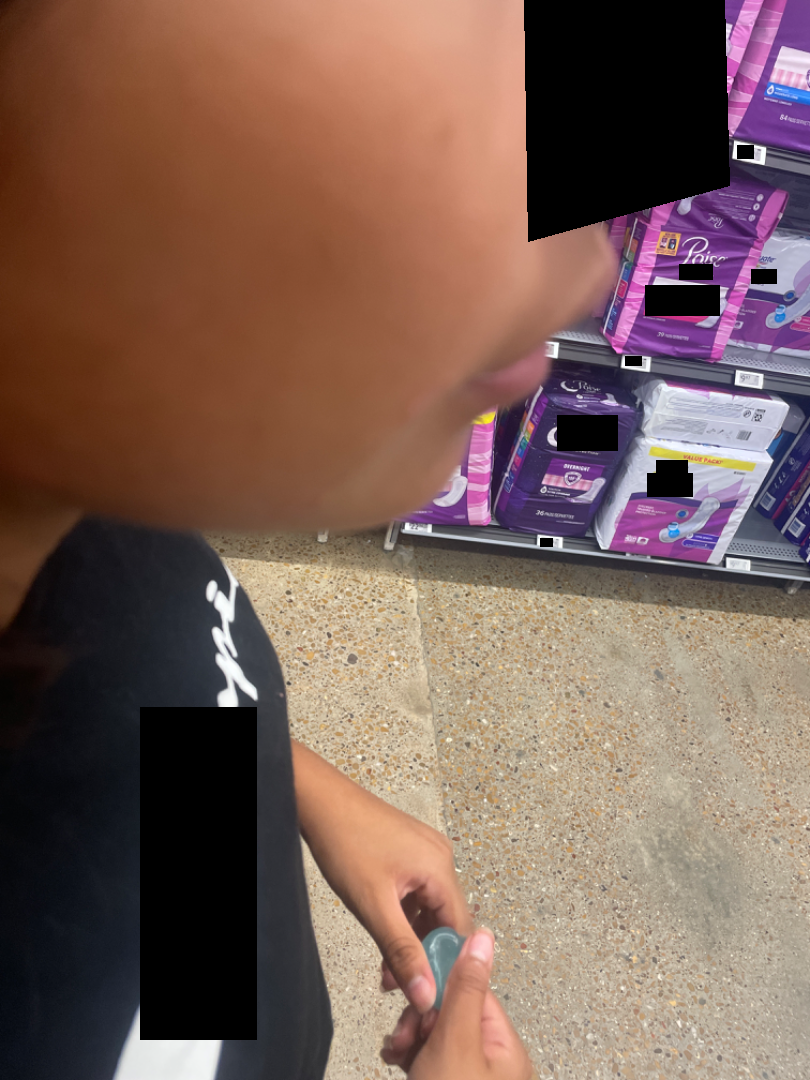Findings:
The skin findings could not be characterized from the image.
Background:
The photograph was taken at an angle. Skin tone: Fitzpatrick phototype IV.